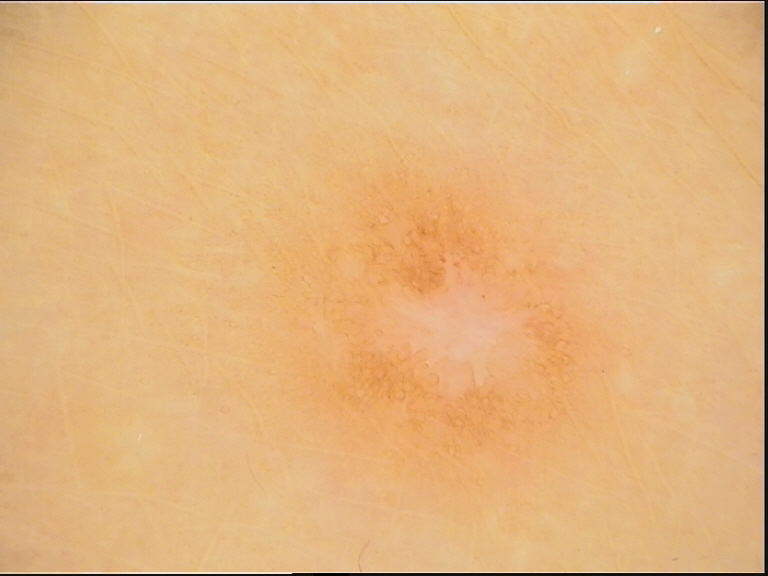imaging: dermoscopy; diagnosis: dermatofibroma (expert consensus).